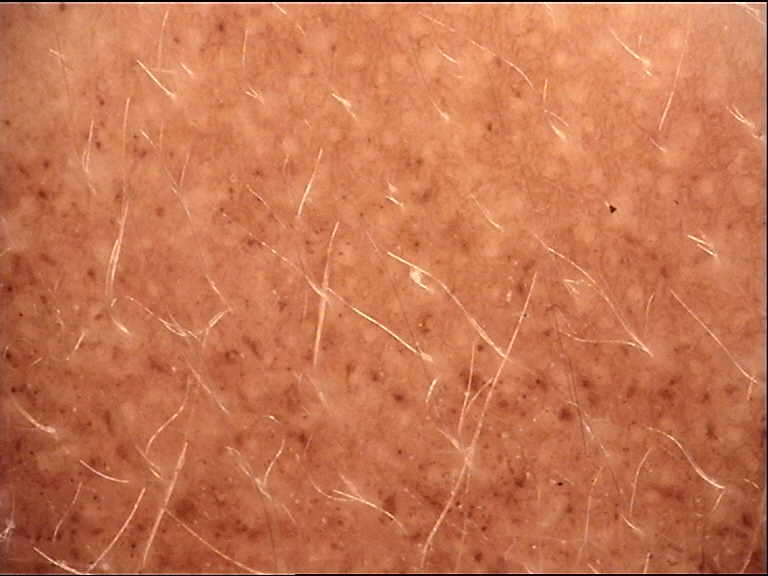diagnostic label = congenital junctional nevus (expert consensus)